Dermoscopy of a skin lesion.
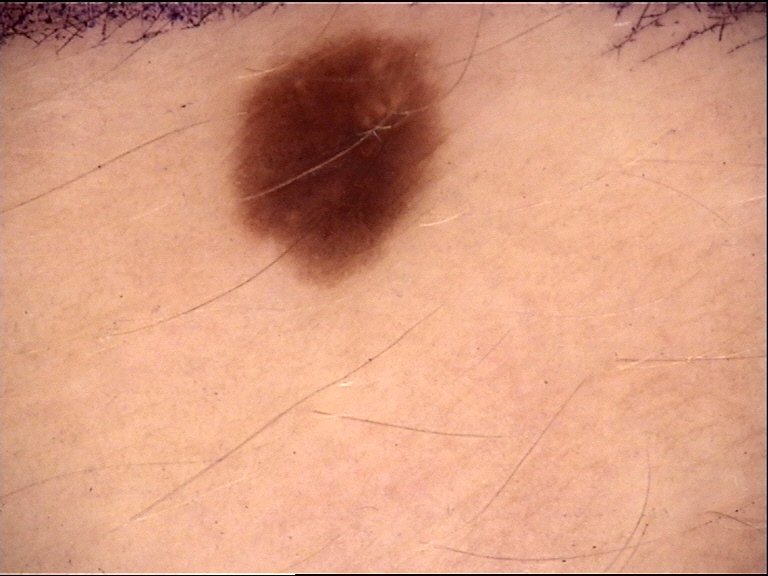label = dysplastic junctional nevus (expert consensus).